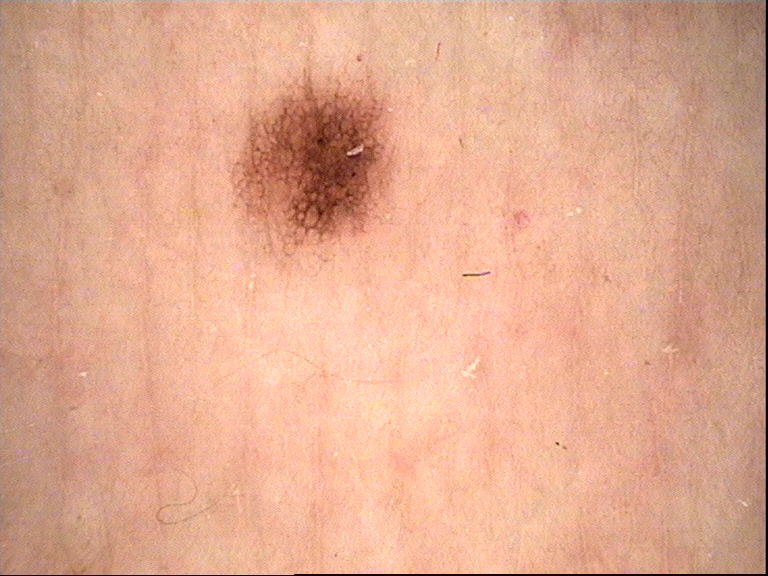Consistent with a benign lesion — a dysplastic junctional nevus.